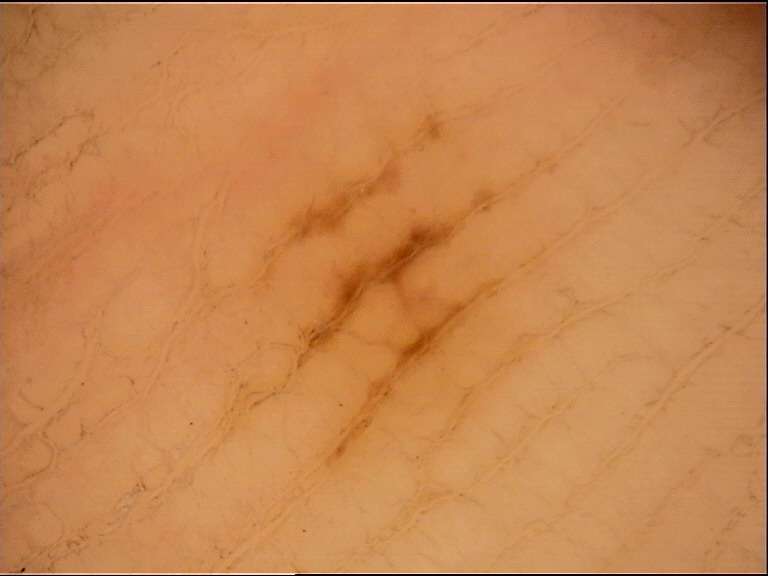A dermatoscopic image of a skin lesion.
Labeled as a banal lesion — an acral junctional nevus.